The contributor is 40–49, female; located on the back of the torso and front of the torso; the photograph was taken at a distance — 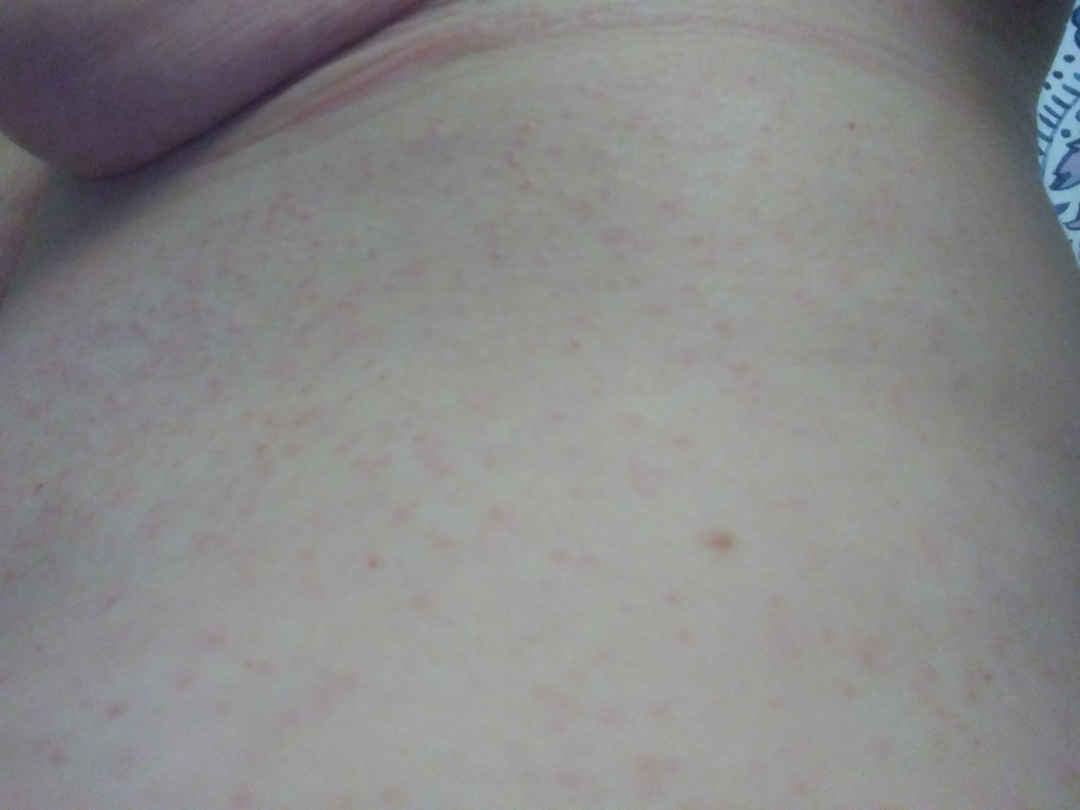The patient described the issue as a rash.
Symptoms reported: itching.
Present for about one day.
On photographic review by a dermatologist, Drug Rash (33%); Viral Exanthem (33%); Hypersensitivity (33%).